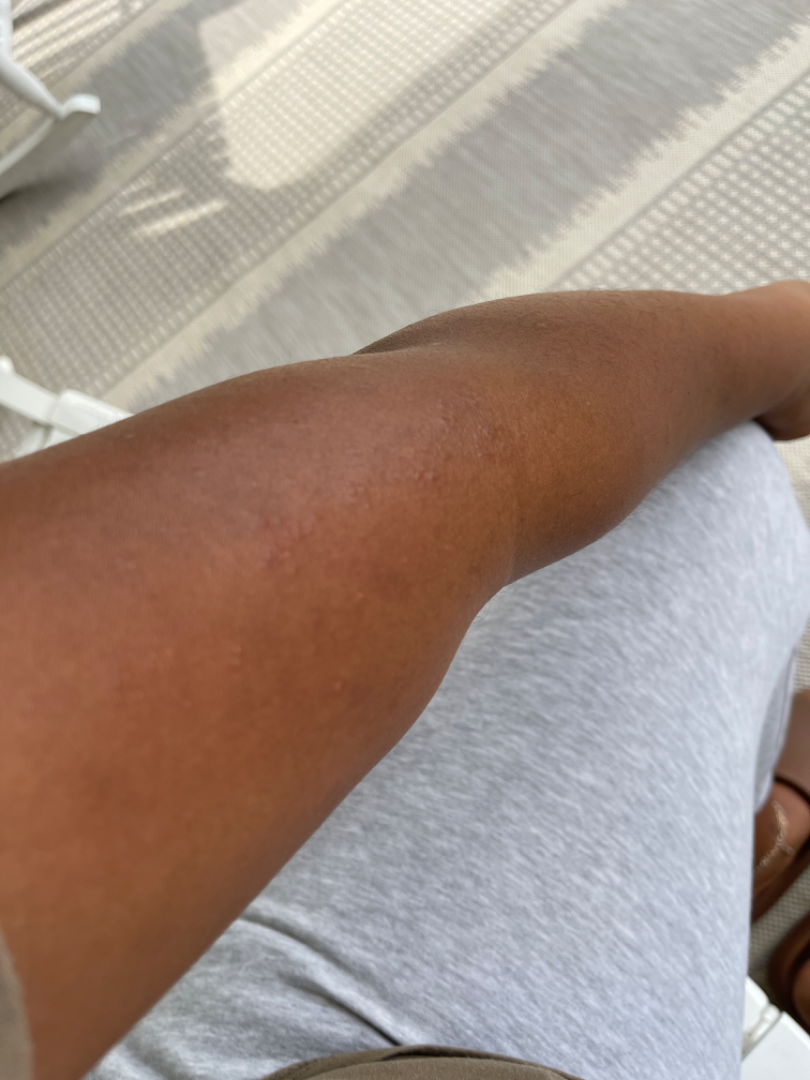assessment: ungradable on photographic review
shot type: at an angle